The subject is a male aged approximately 65 · a dermoscopy image of a single skin lesion — 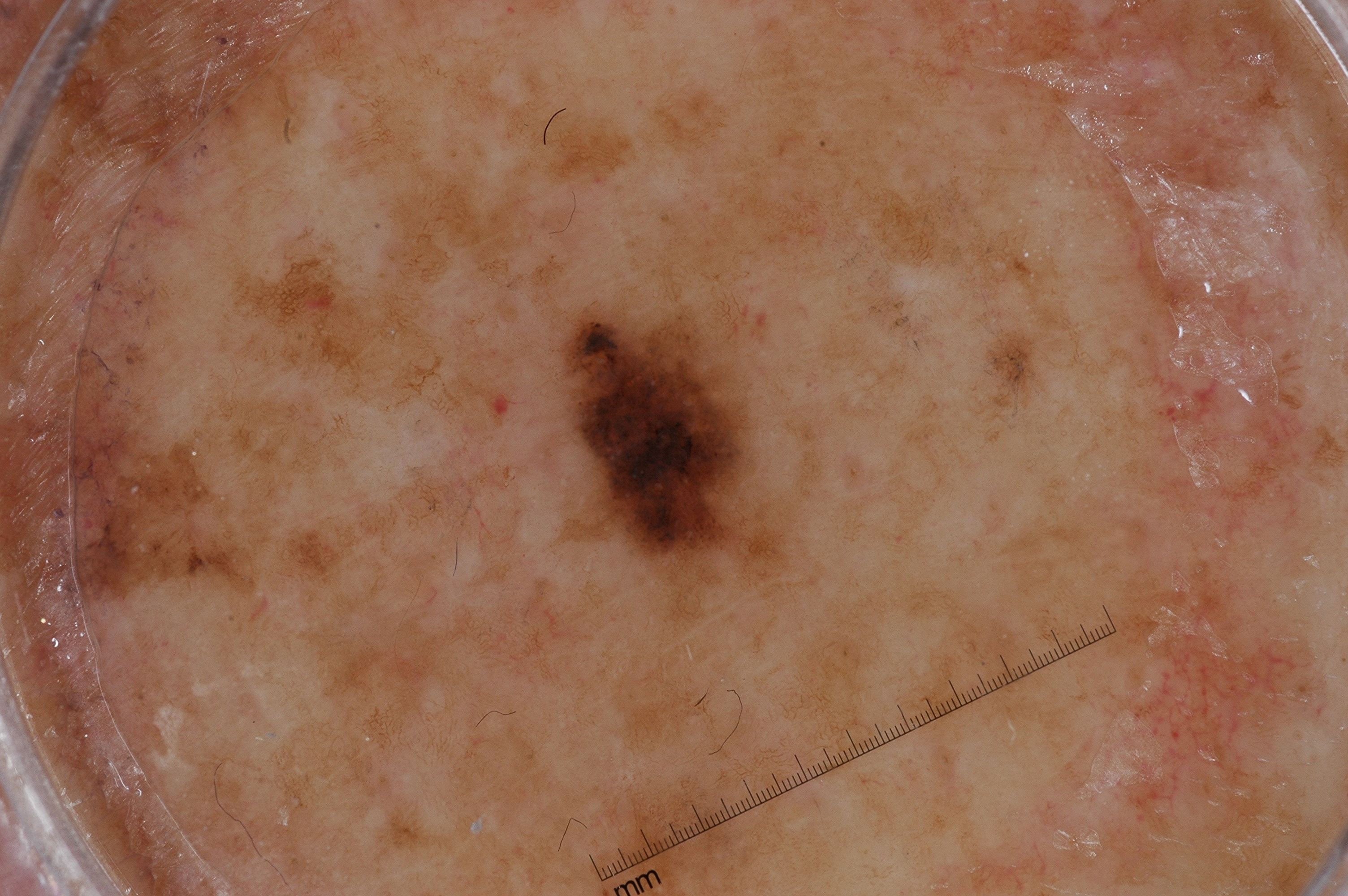lesion extent: small; bounding box: box(555, 283, 759, 569); absent dermoscopic findings: pigment network, streaks, negative network, and milia-like cysts; diagnostic label: a melanocytic nevus.